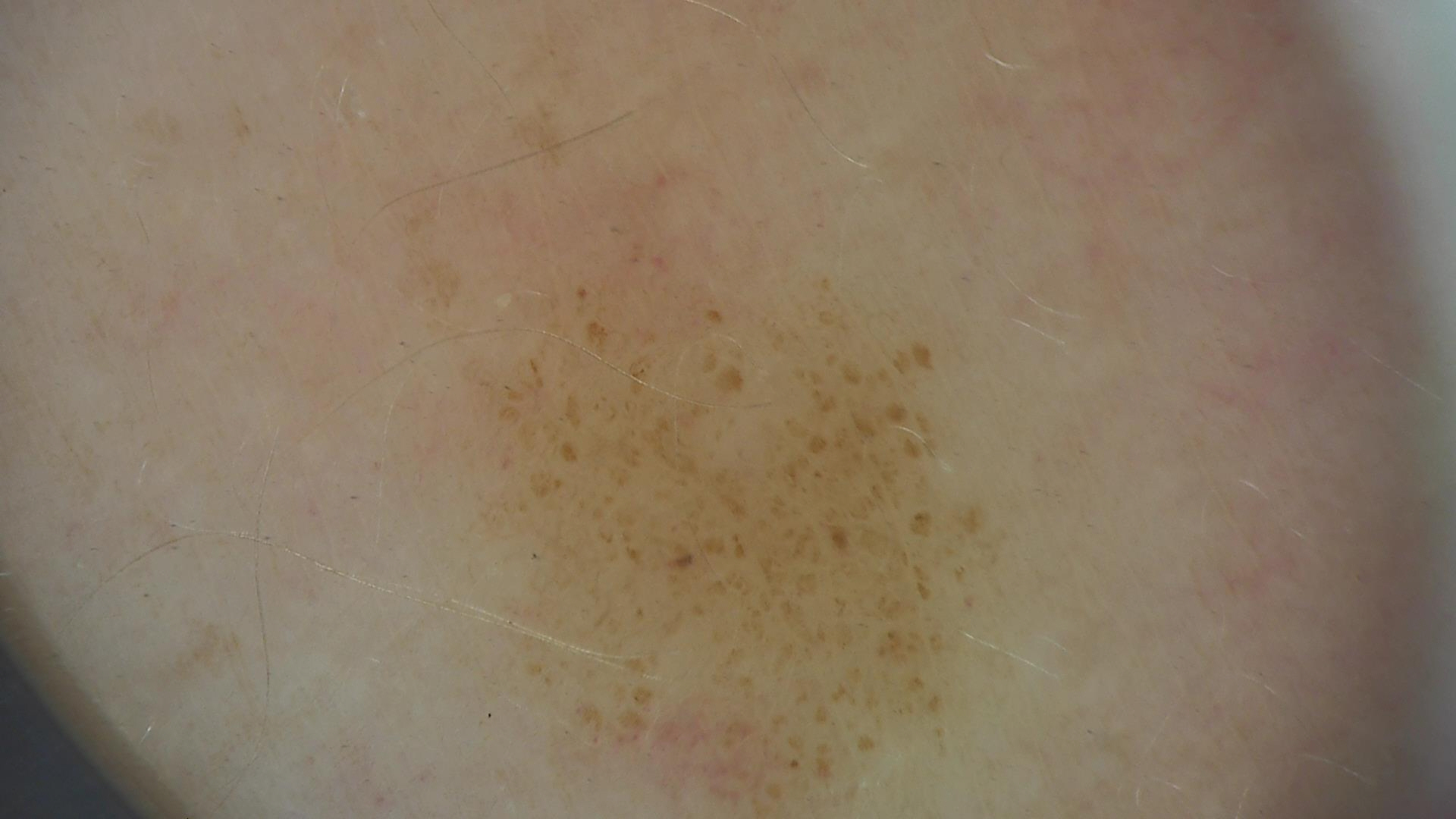Summary:
A dermoscopic photograph of a skin lesion.
Impression:
Diagnosed as a benign lesion — a dysplastic junctional nevus.